The patient says their skin reddens with sun exposure; a clinical photograph of a skin lesion; a male subject aged 60 — 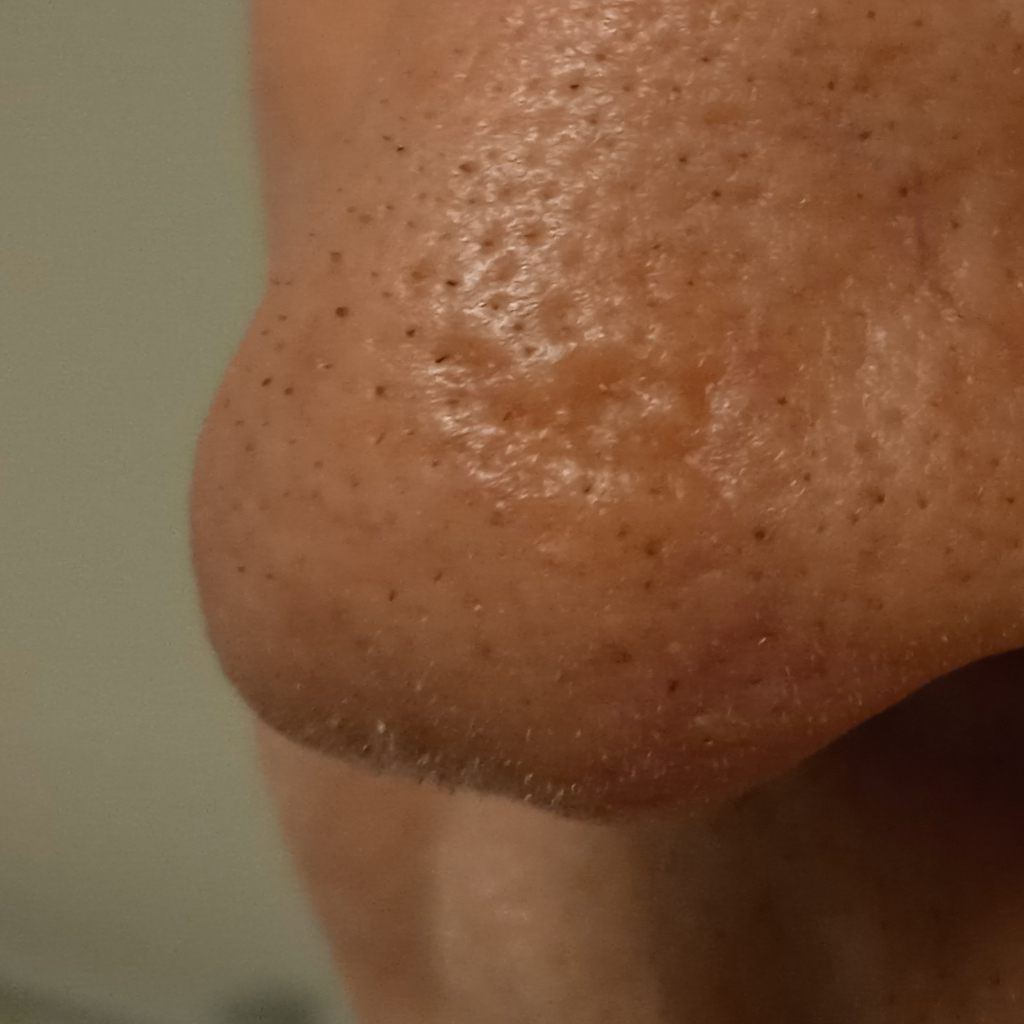Clinical context: The lesion is about 8.5 mm across. Pathology: On biopsy, the diagnosis was a basal cell carcinoma, following excision, with tumor thickness 1.7 mm.